The affected area is the top or side of the foot; female contributor, age 50–59; the photograph is a close-up of the affected area:
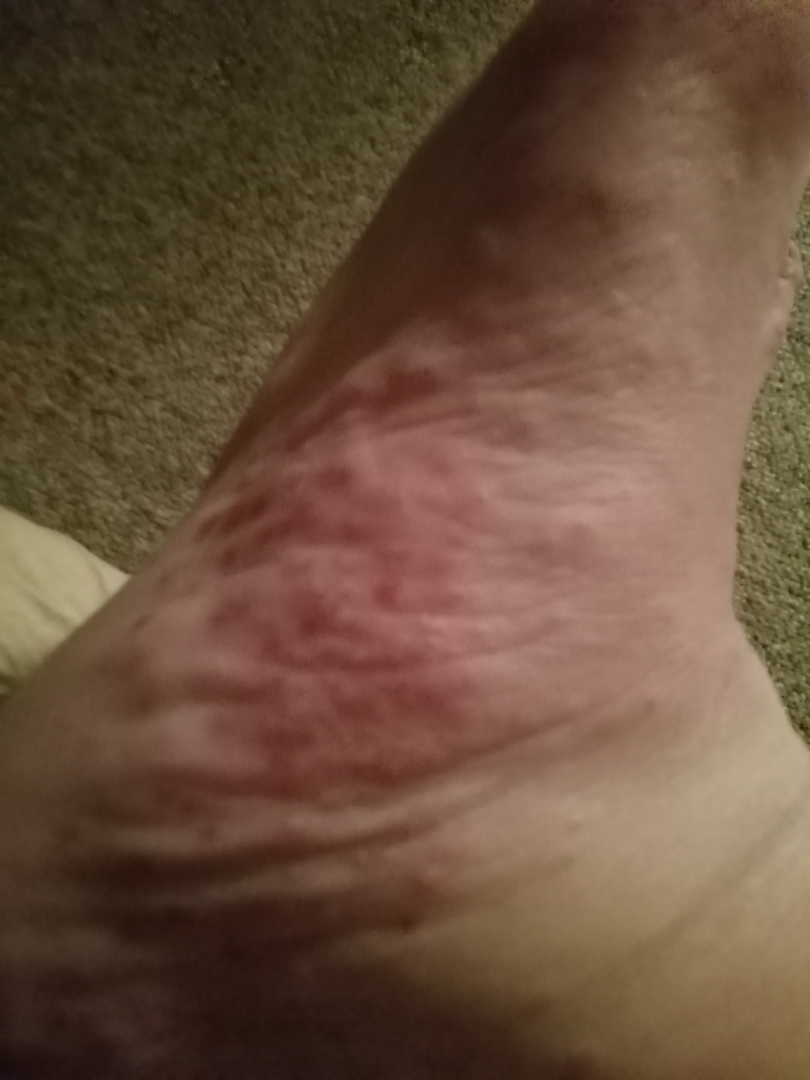Impression: Three dermatologists independently reviewed the case: most likely Eczema; also on the differential is Tinea; an alternative is Psoriasis; a remote consideration is Scabies.